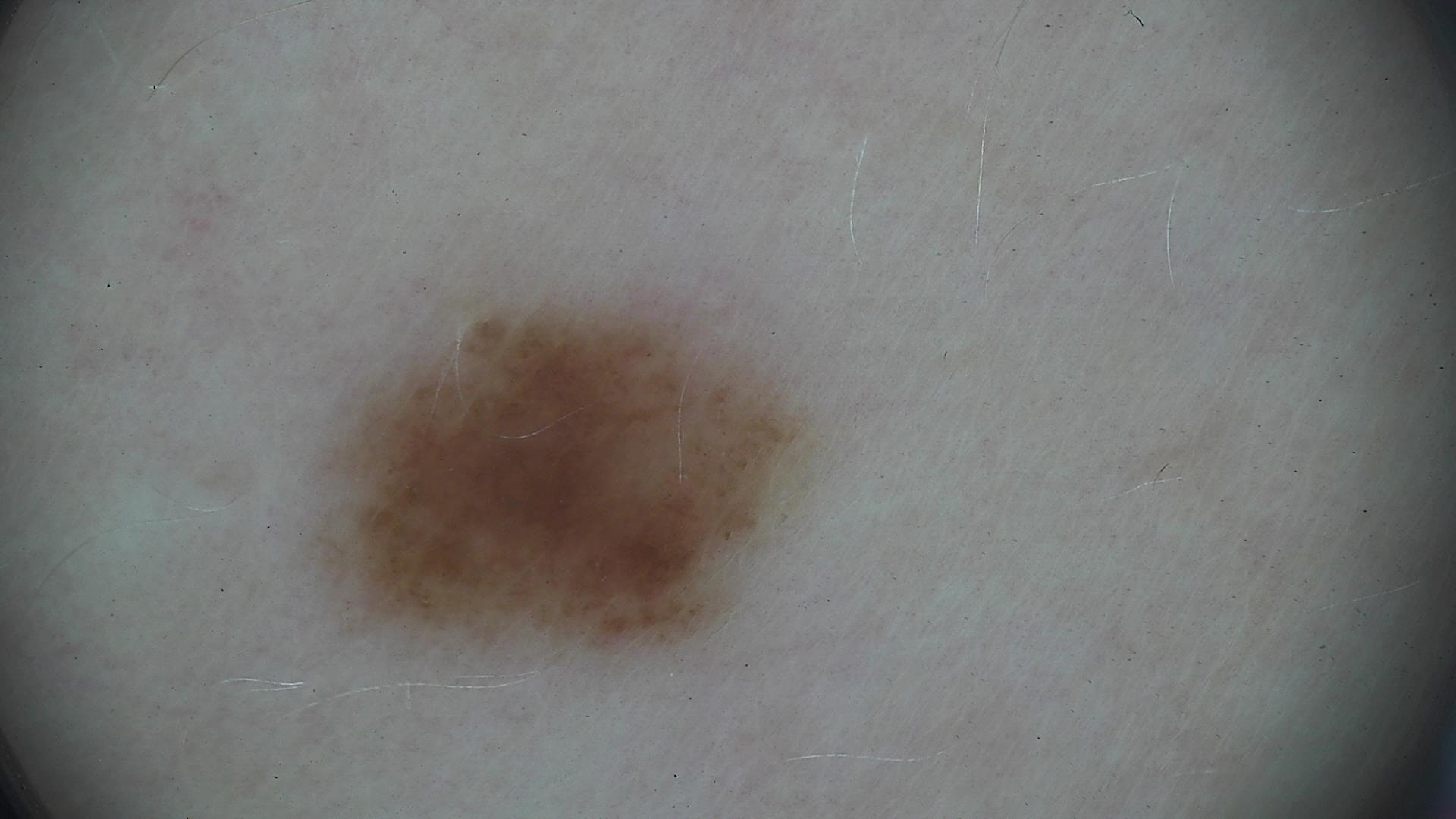Q: What is the imaging modality?
A: dermatoscopy
Q: What is the diagnosis?
A: dysplastic junctional nevus (expert consensus)